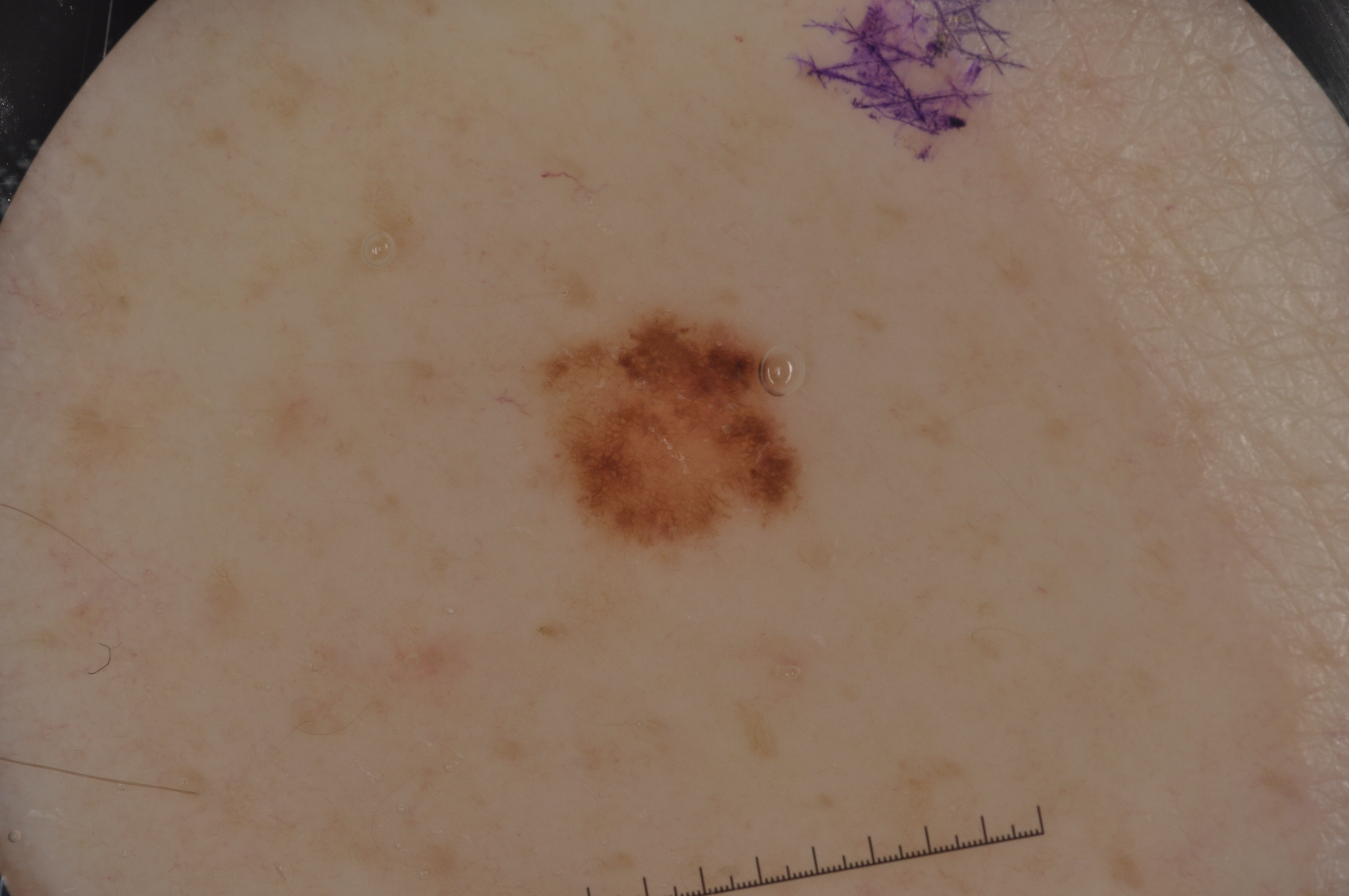Summary:
A male patient, about 55 years old. A dermoscopic image of a skin lesion. A small lesion occupying a minor part of the field. As (left, top, right, bottom), the lesion is bounded by 538 315 801 553. Dermoscopic review identifies pigment network; no streaks, milia-like cysts, or negative network.
Impression:
Consistent with a melanocytic nevus.